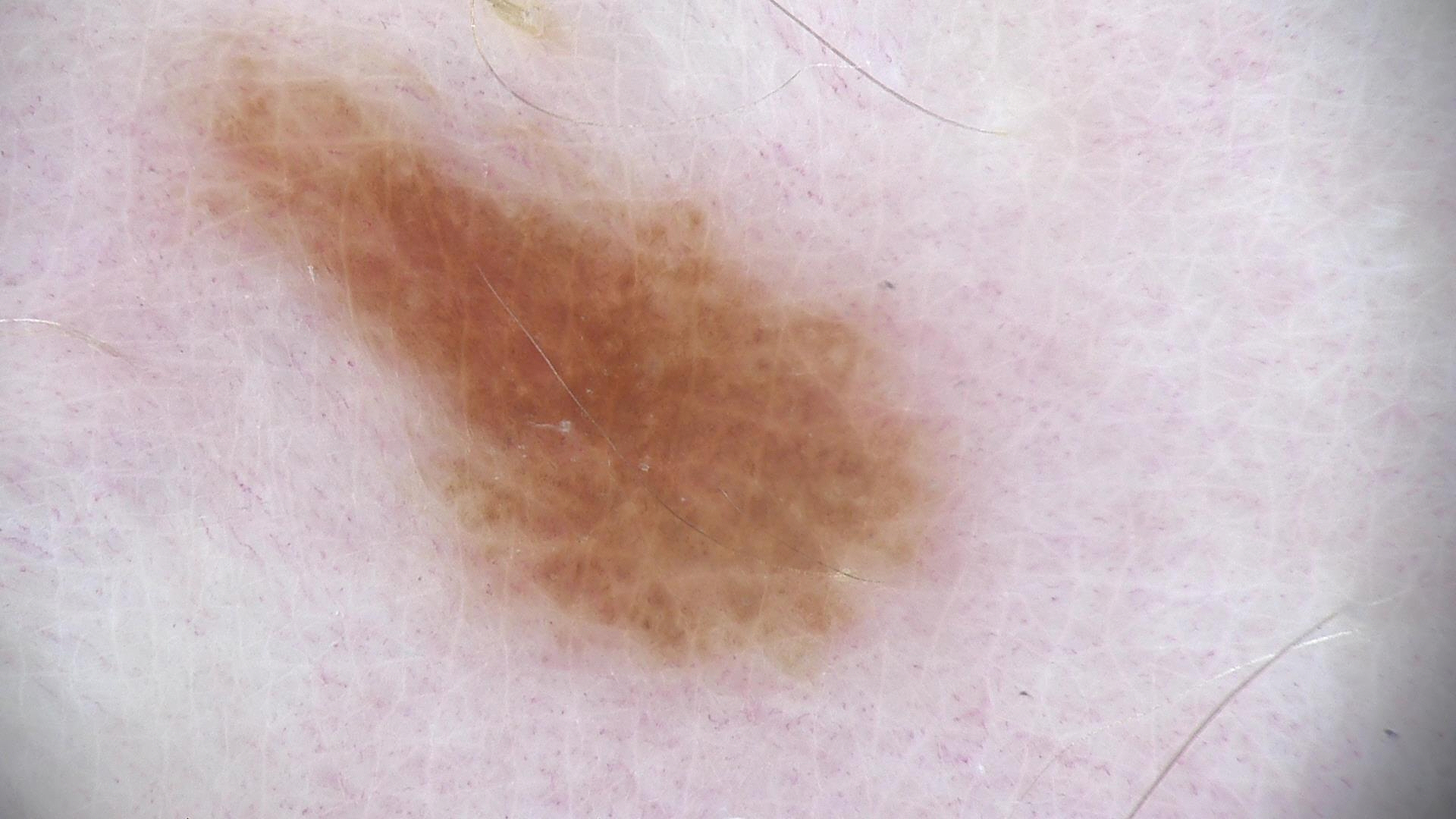A dermoscopic image of a skin lesion. The diagnosis was a dysplastic junctional nevus.